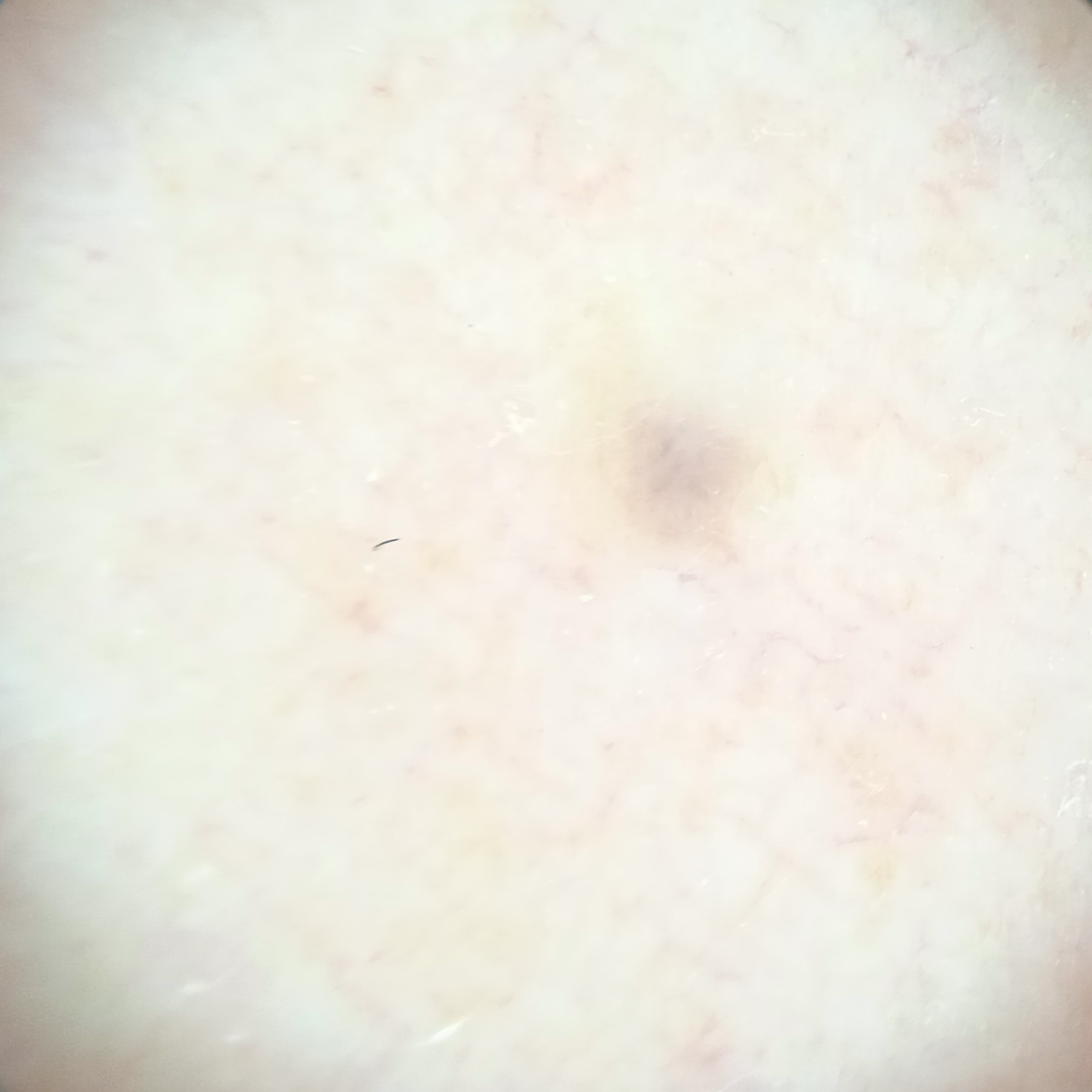subject = female, age 48; relevant history = a history of sunbed use, a family history of skin cancer; nevus count = few melanocytic nevi overall; image = dermatoscopic image; sun reaction = skin reddens painfully with sun exposure; diameter = 1.8 mm; assessment = melanocytic nevus (dermatologist consensus).